Present for less than one week. The patient is a female aged 40–49. The patient notes the lesion is raised or bumpy. The patient notes bothersome appearance, enlargement and itching. Located on the leg and arm. The photograph was taken at an angle. The patient considered this a rash:
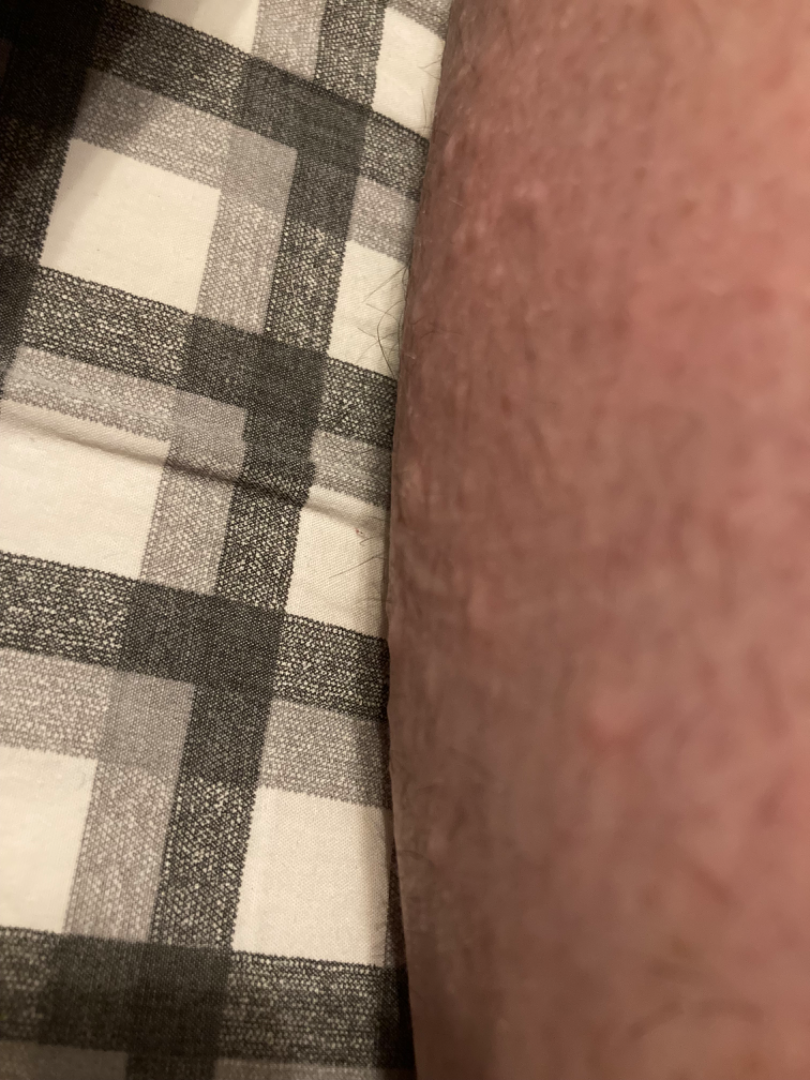  differential:
    leading:
      - Urticaria
    considered:
      - Eczema
      - Insect Bite